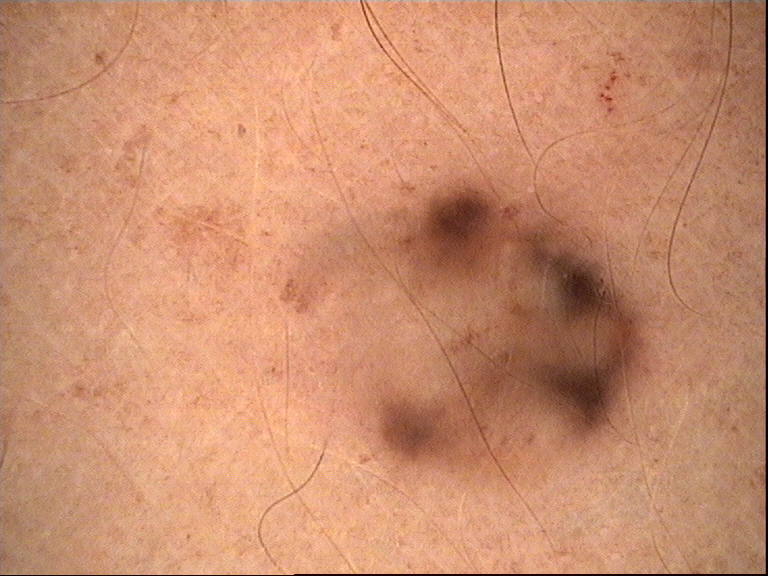label: blue nevus (expert consensus).